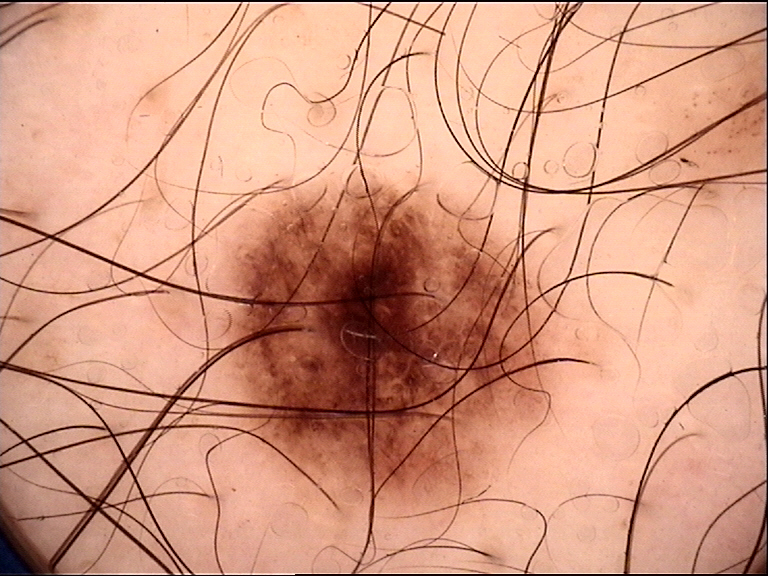image type: dermoscopy
diagnosis: dysplastic junctional nevus (expert consensus)